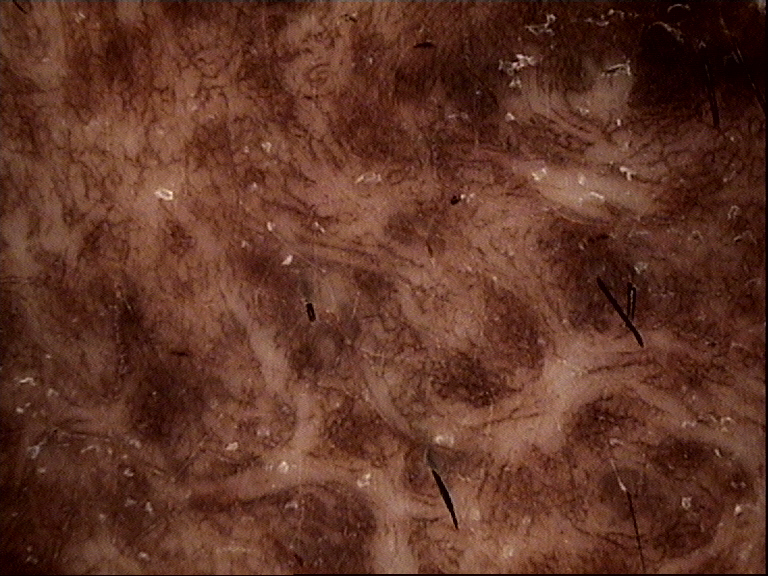The diagnosis was a banal lesion — a congenital compound nevus.